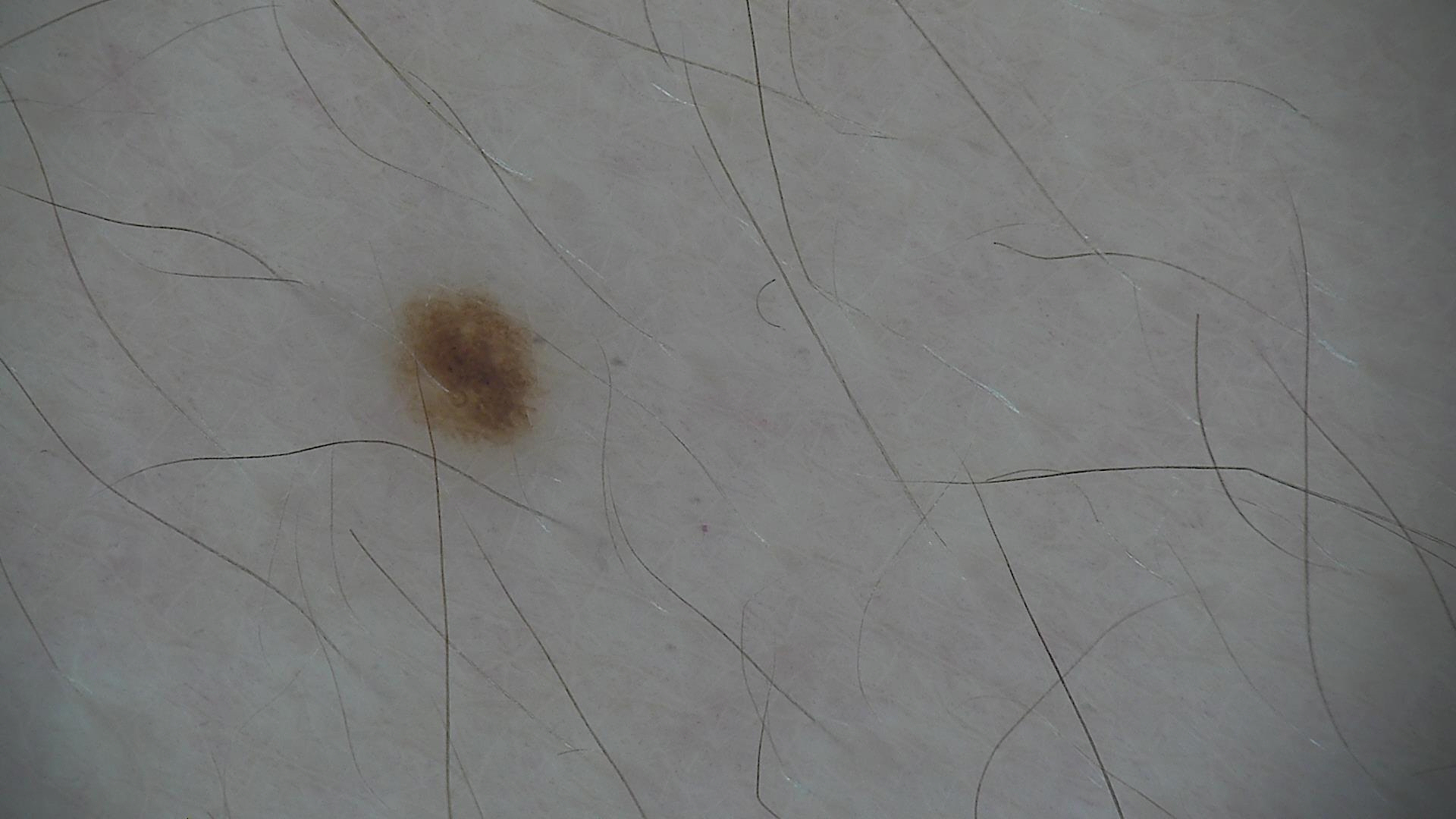image type — dermoscopy
classification — banal
assessment — junctional nevus (expert consensus)